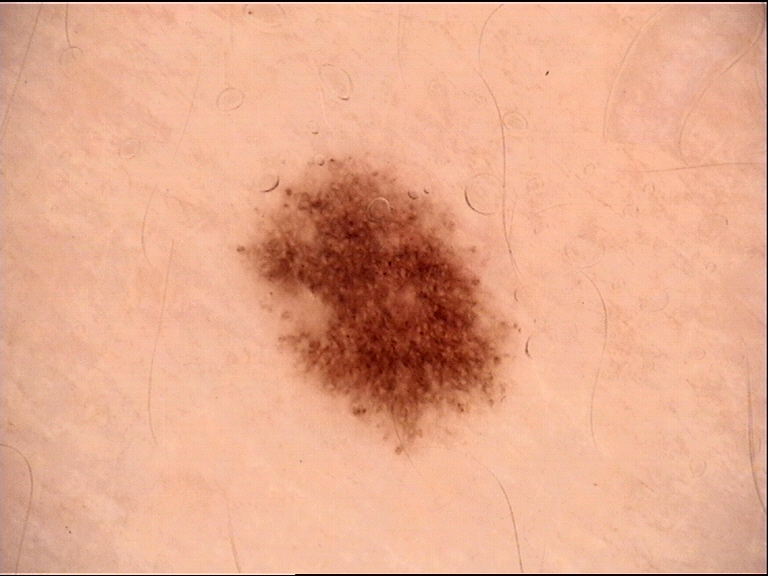The diagnosis was a dysplastic junctional nevus.